The patient reports the condition has been present for about one day · close-up view · the patient reports the lesion is flat · self-categorized by the patient as a nail problem · associated systemic symptoms include shortness of breath and joint pain · the subject is female: 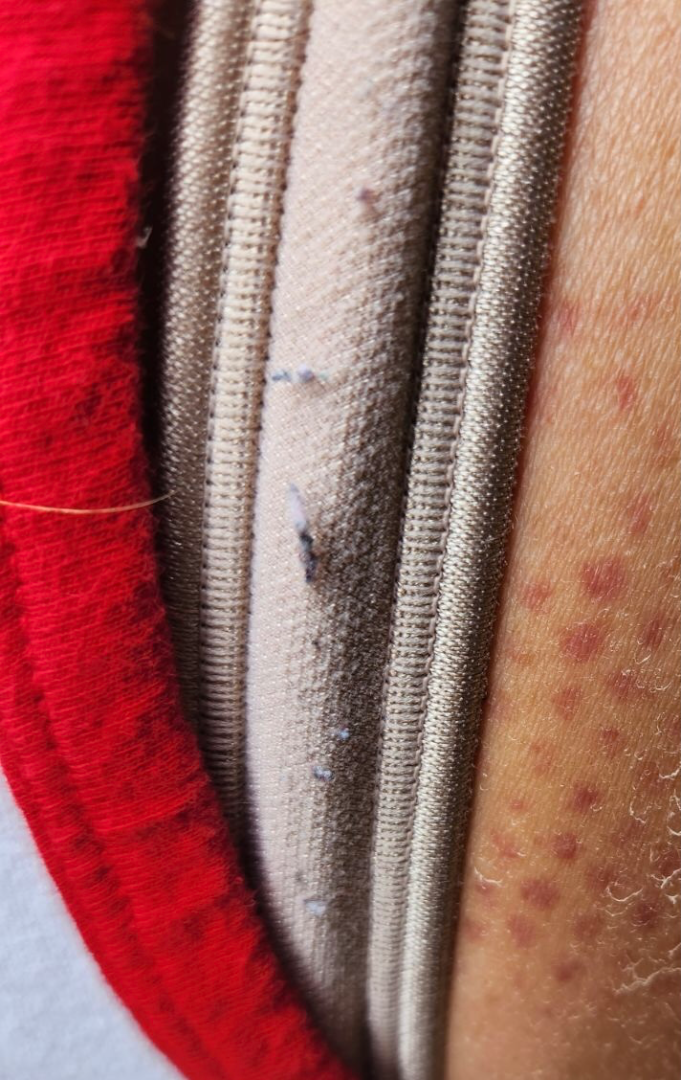Findings:
Consistent with ecchymoses.